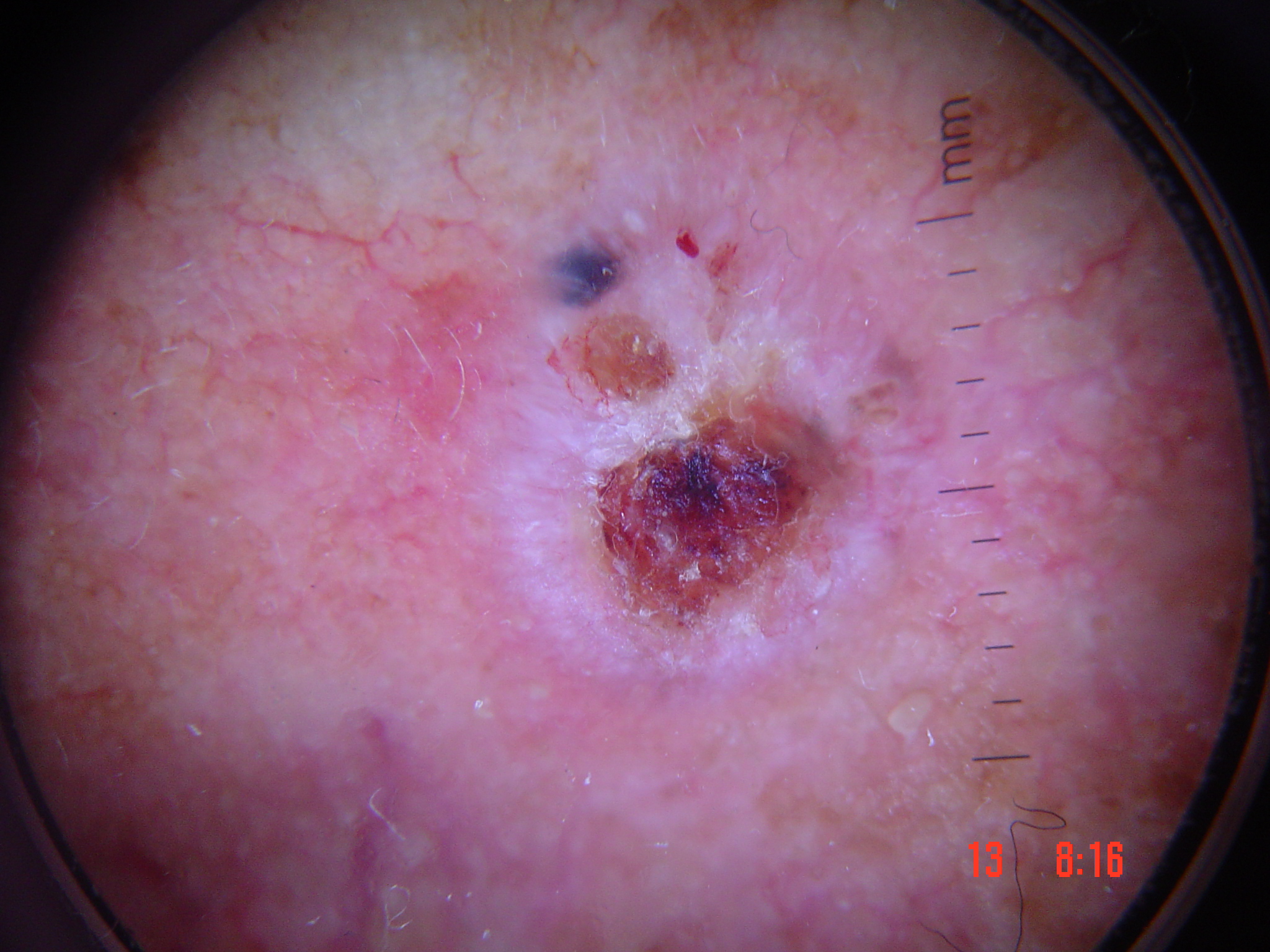Q: What is the diagnosis?
A: basal cell carcinoma (biopsy-proven)